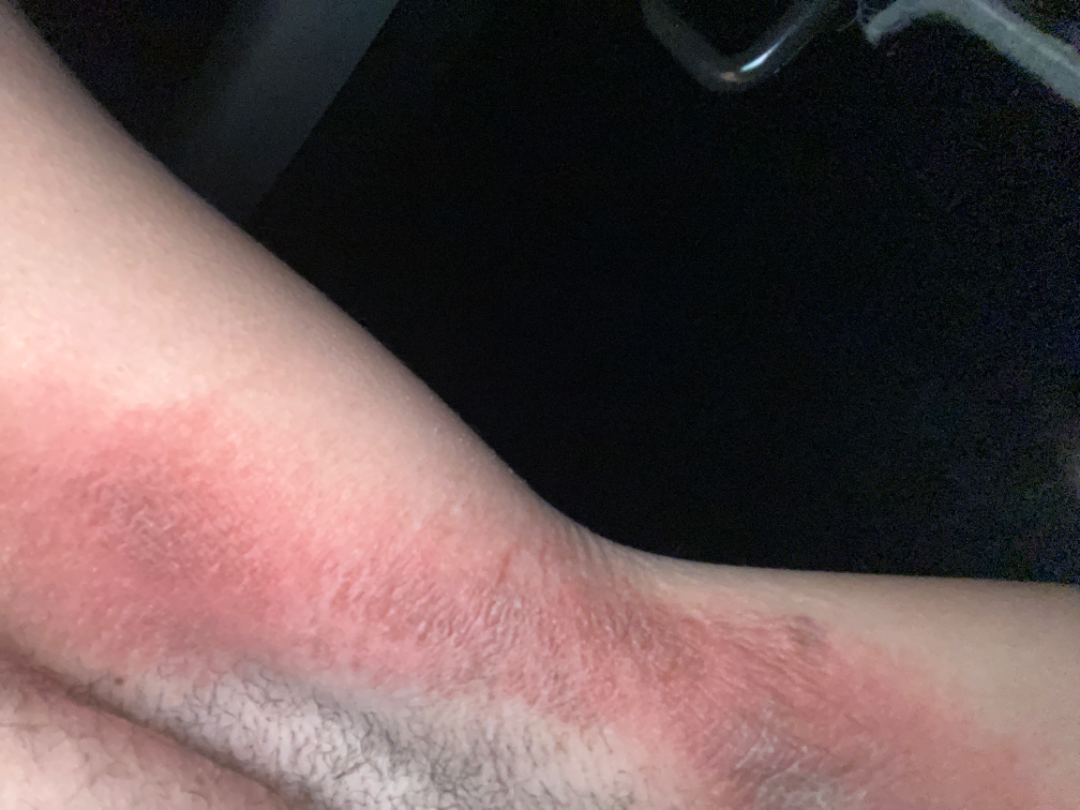Impression:
The image was not sufficient for the reviewer to characterize the skin condition.
History:
Fitzpatrick phototype II; non-clinician graders estimated Monk Skin Tone 3 (US pool) or 2 (India pool). Close-up view.